A skin lesion imaged with a dermatoscope.
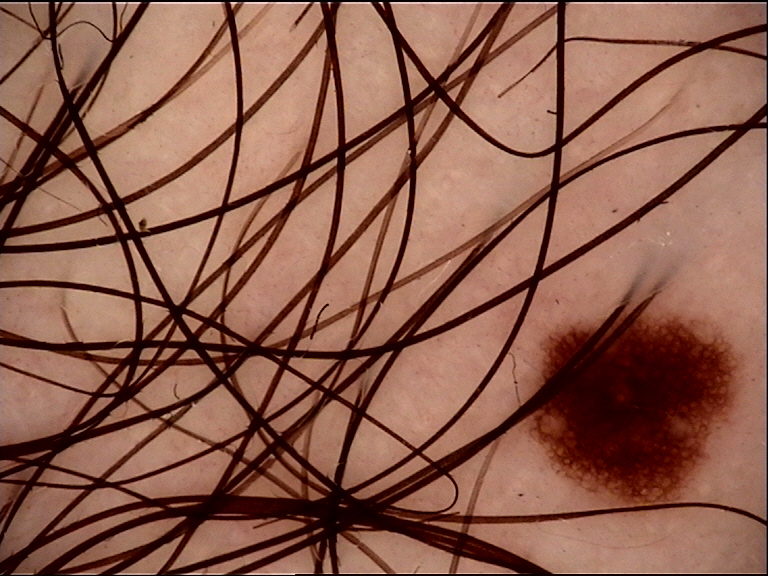Diagnosed as a banal lesion — a junctional nevus.